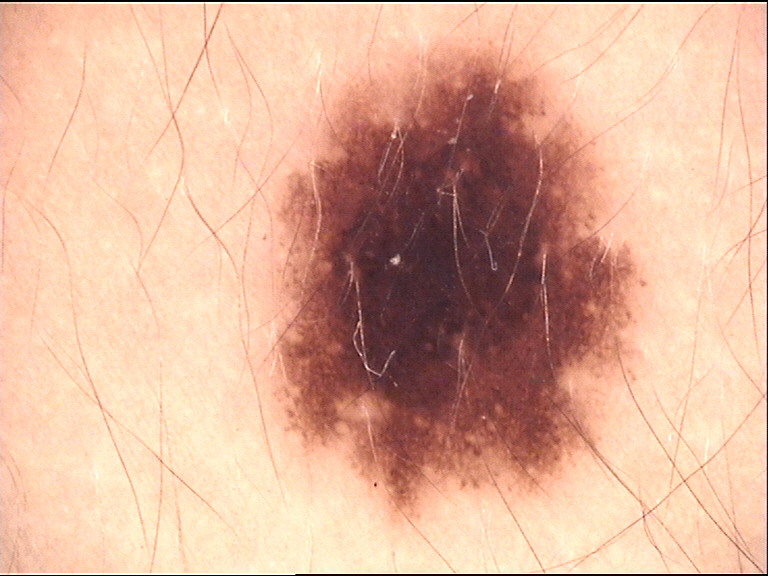diagnostic label: dysplastic junctional nevus (expert consensus).